The photograph was taken at an angle — 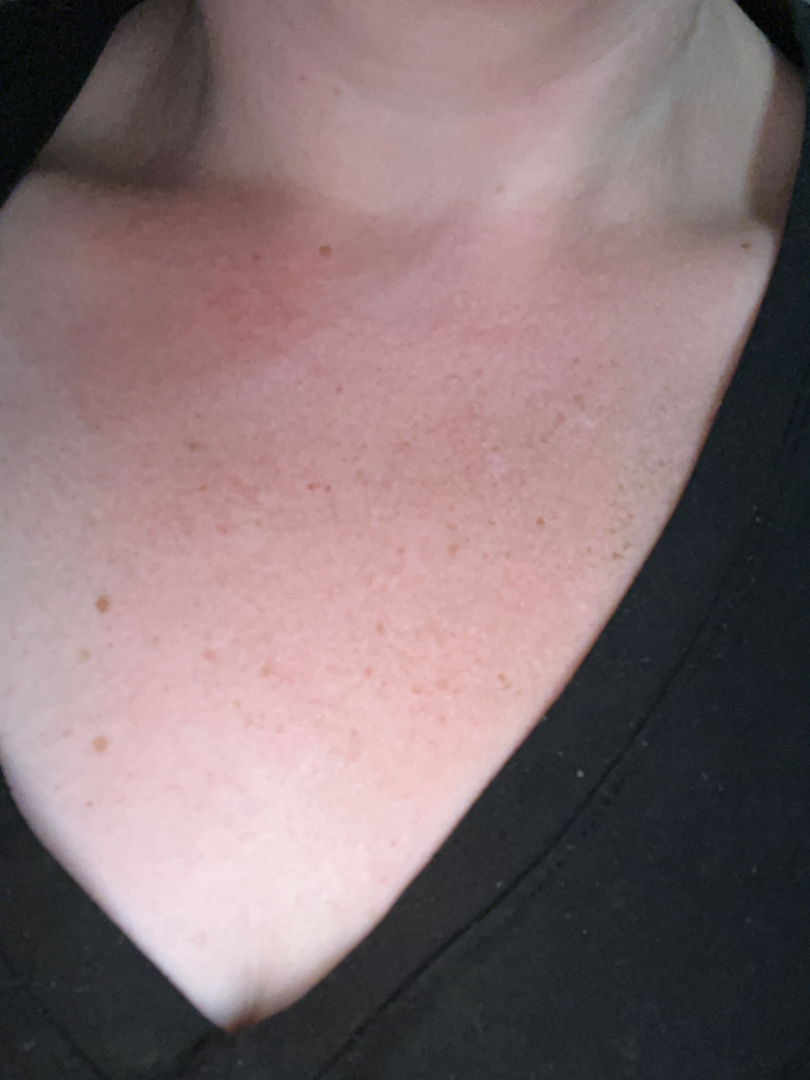Review: No clear dermatological pathology was apparent in the photograph.